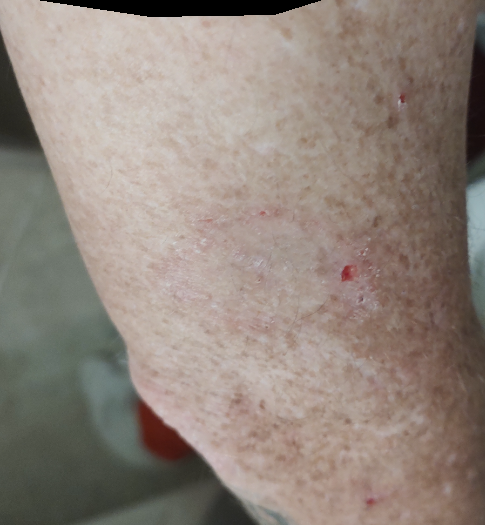The image was not sufficient for the reviewer to characterize the skin condition.